A skin lesion imaged with a dermatoscope.
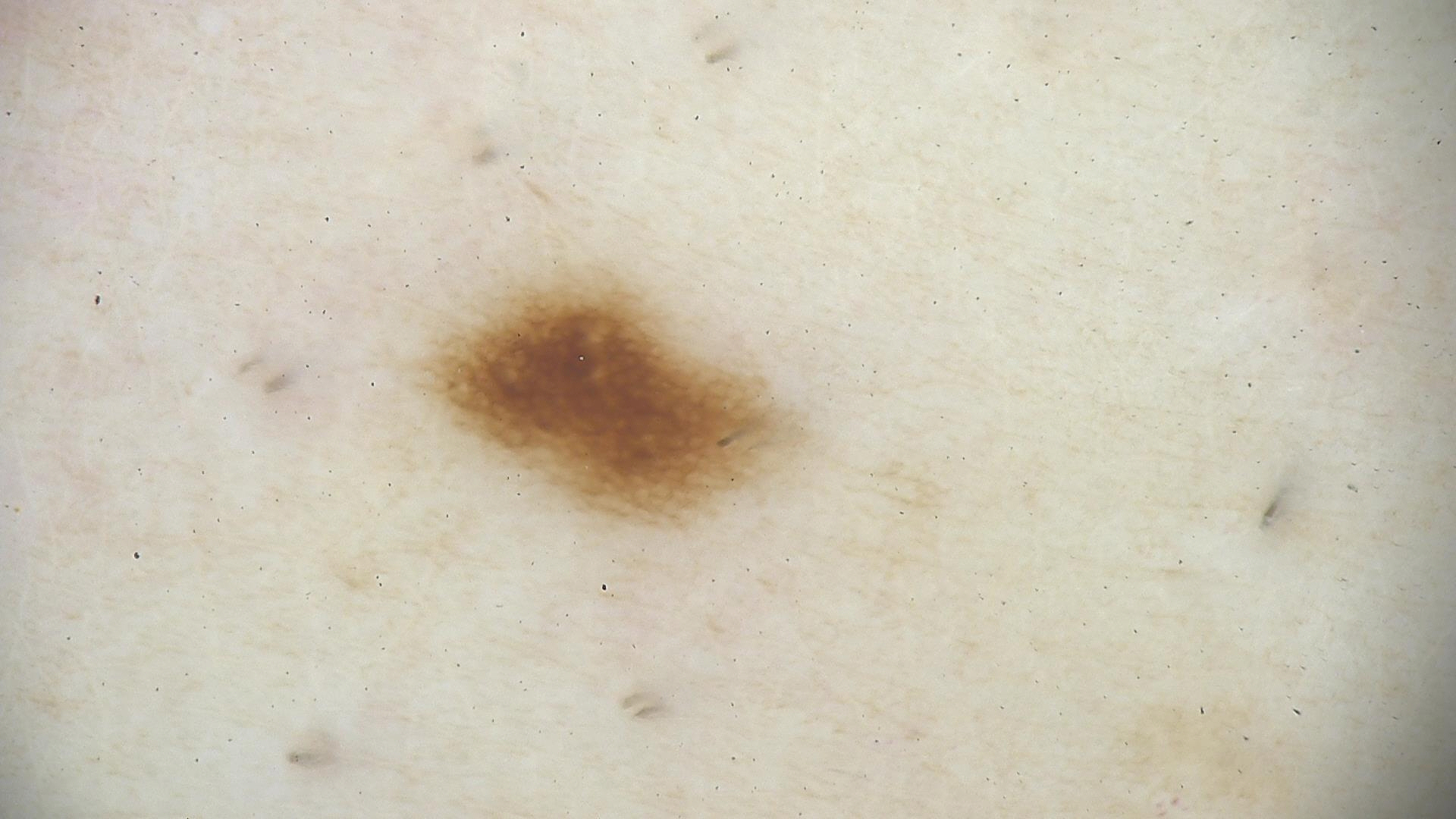assessment=dysplastic junctional nevus (expert consensus).